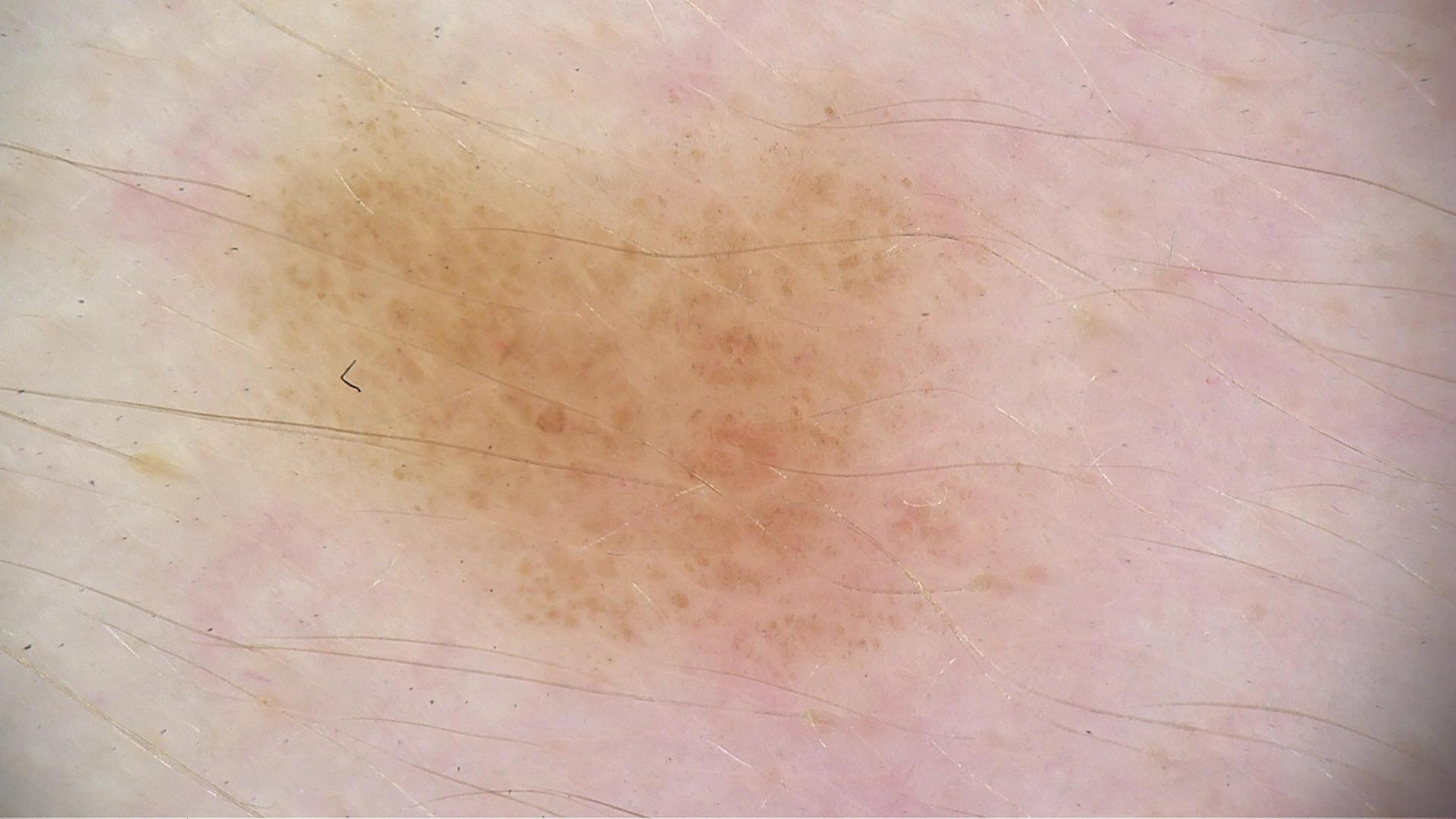Labeled as a dysplastic junctional nevus.